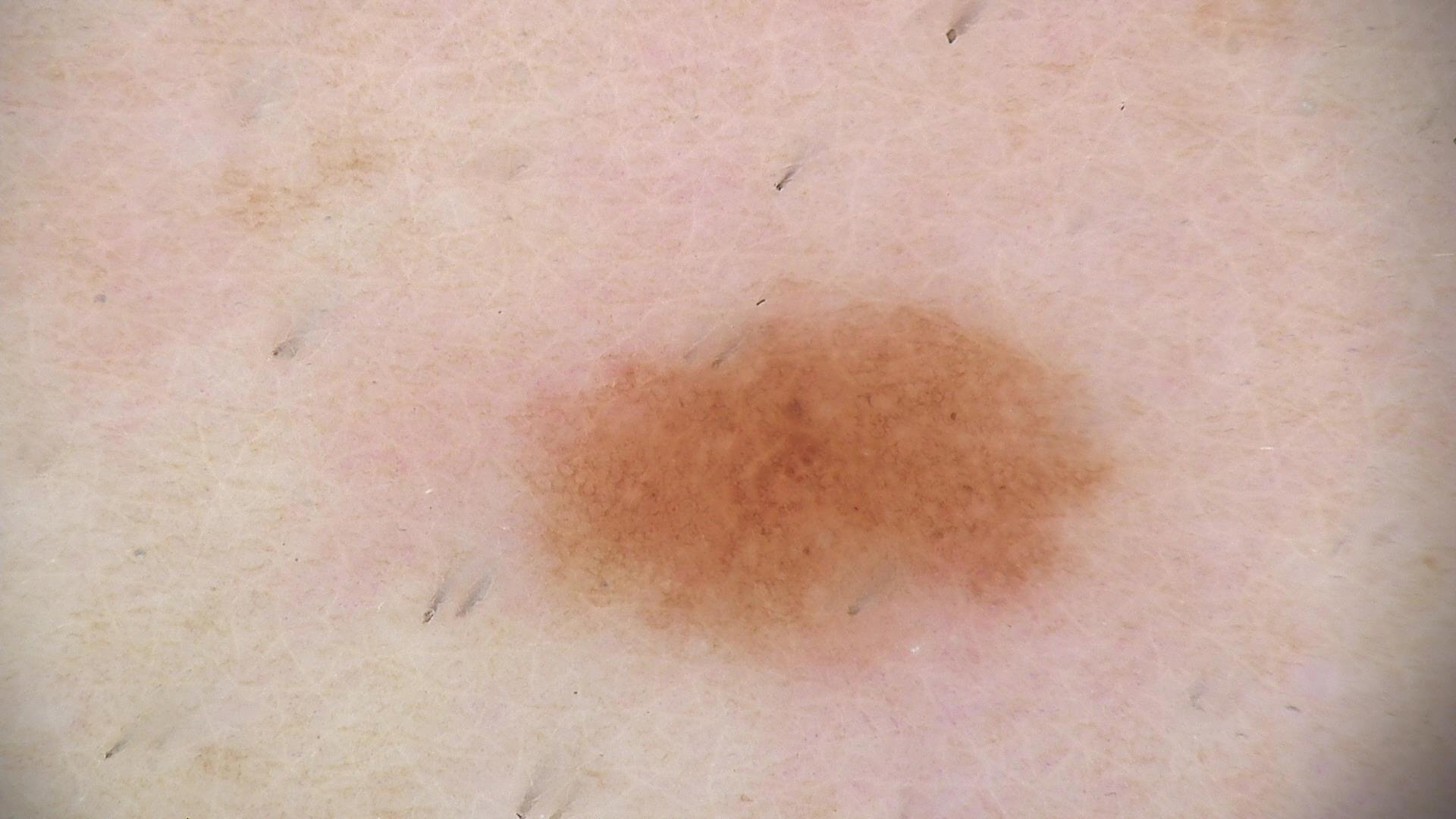assessment = dysplastic junctional nevus (expert consensus).